A dermoscopy image of a single skin lesion, a female subject roughly 40 years of age.
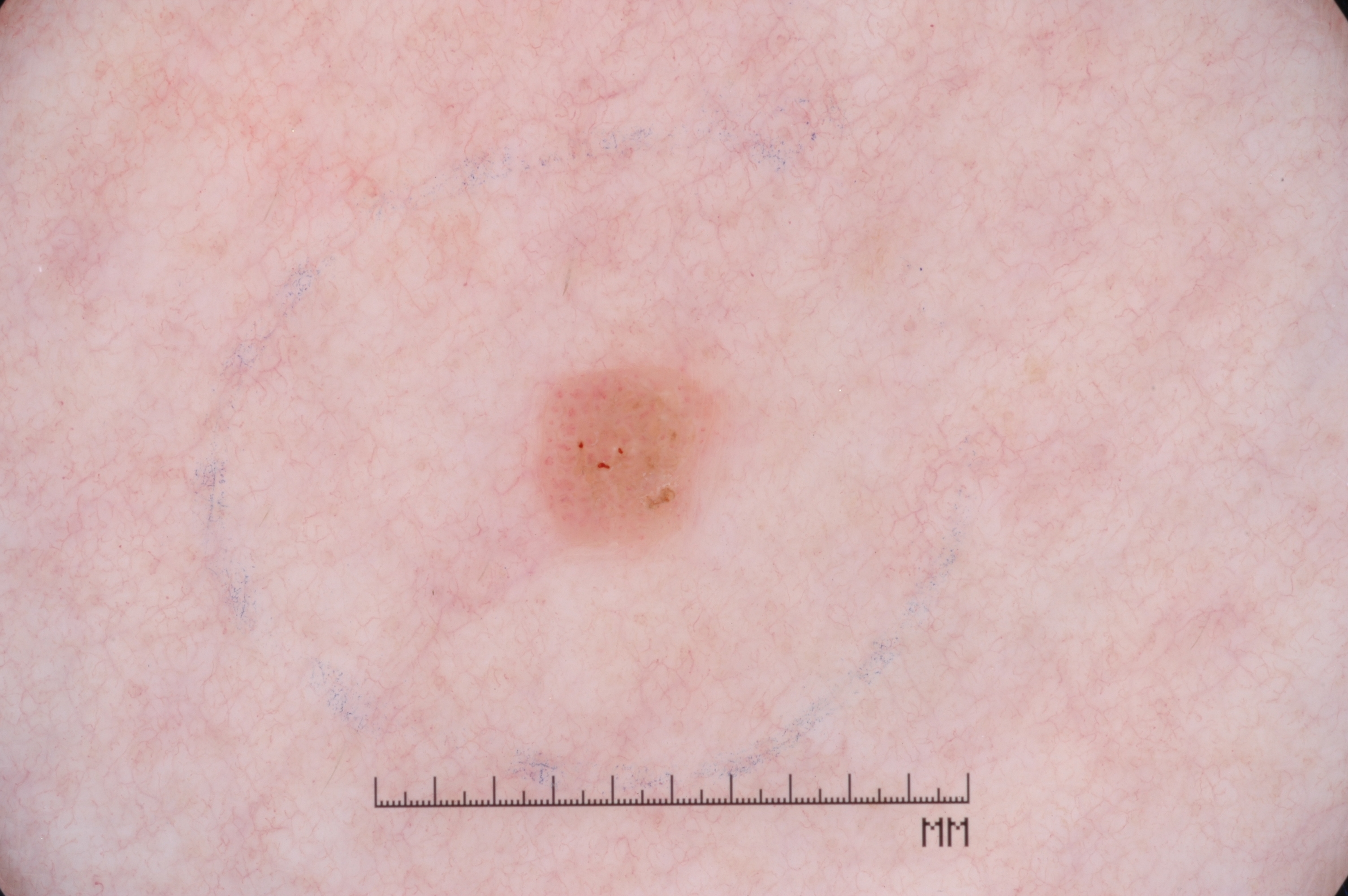Findings:
- dermoscopic pattern — milia-like cysts; absent: negative network, streaks, and pigment network
- location — 527/343/737/553
- lesion extent — ~3% of the field
- assessment — a seborrheic keratosis